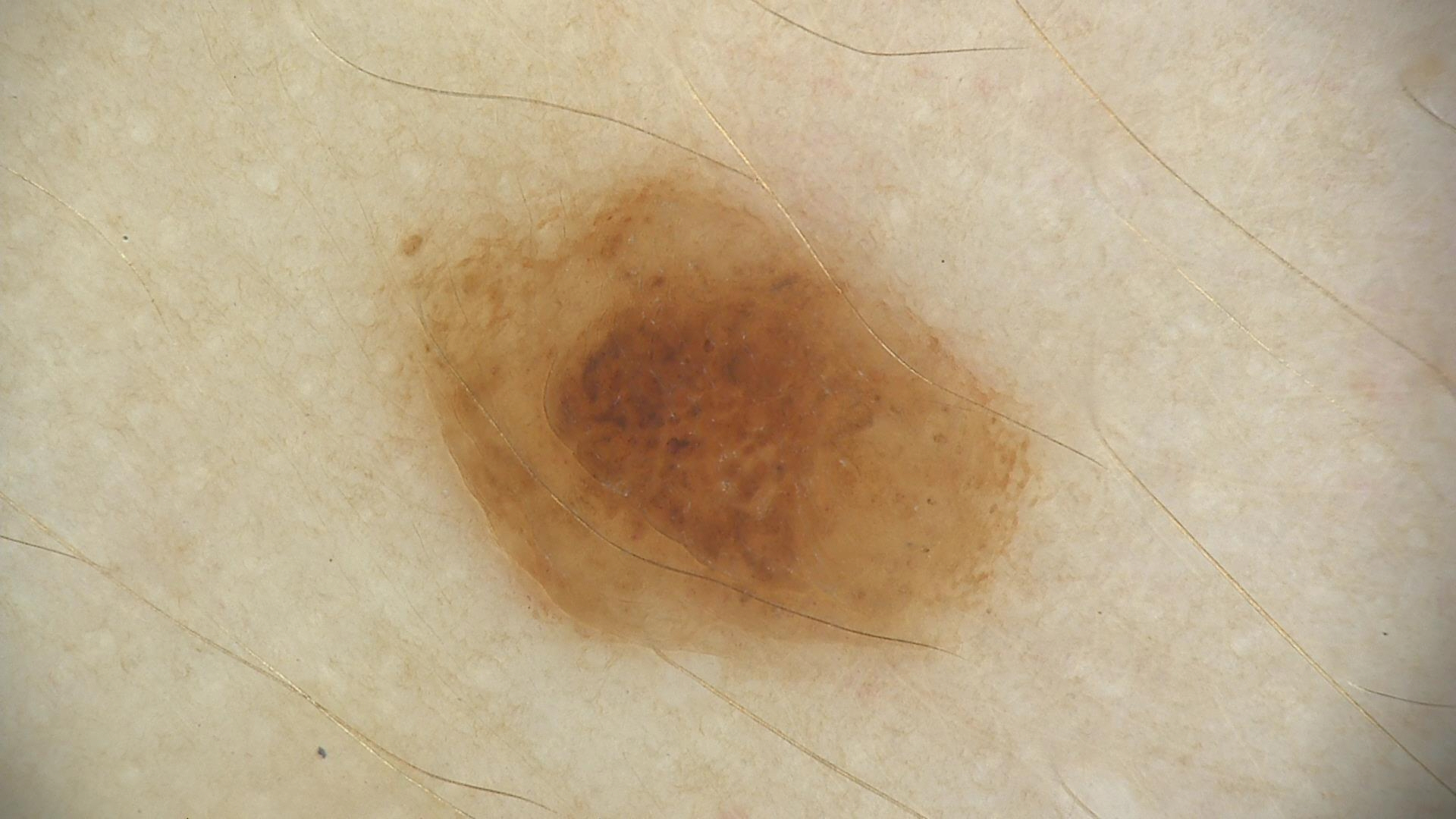Case:
- diagnosis · compound nevus (expert consensus)